A dermoscopic image of a skin lesion — 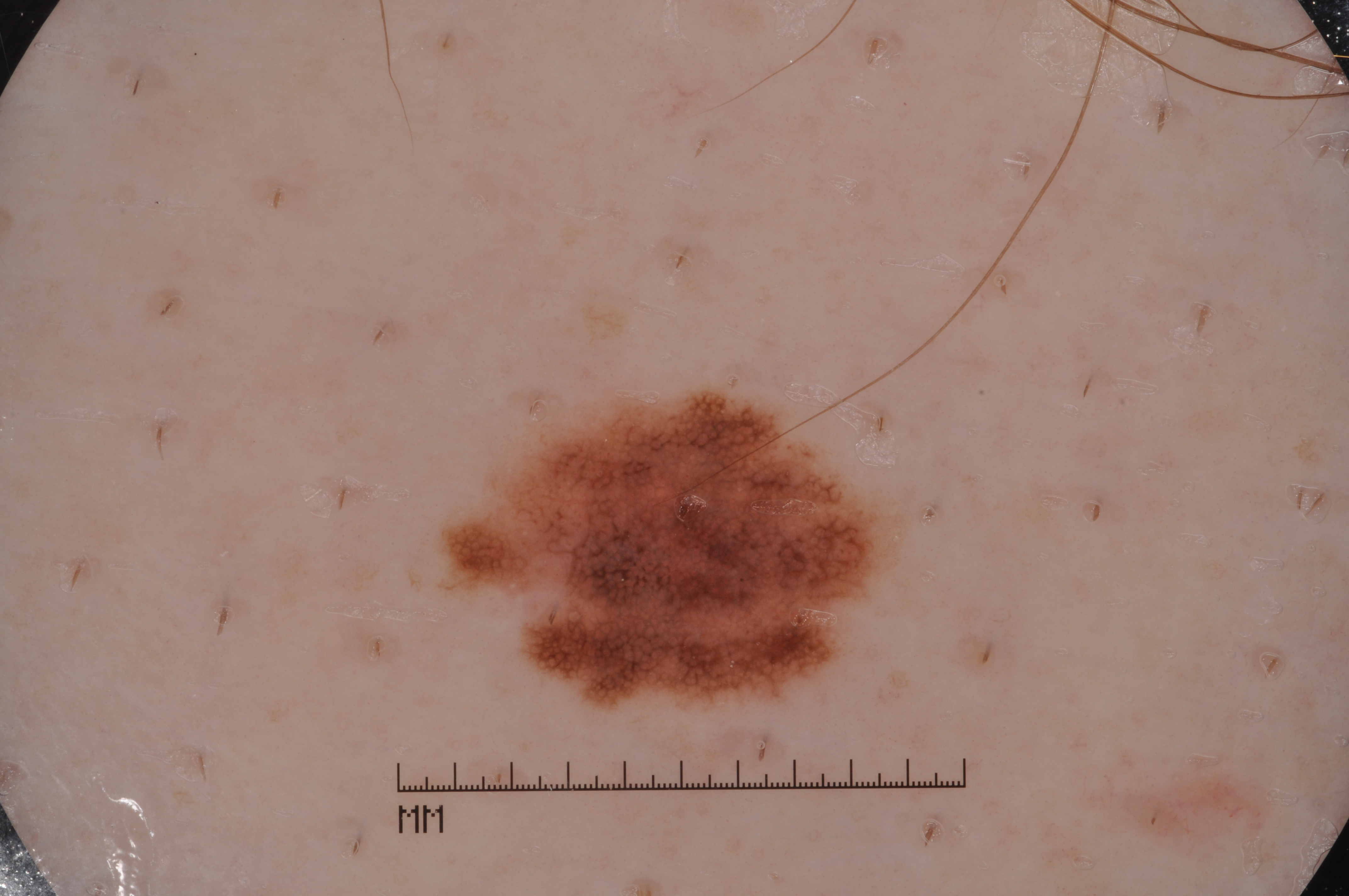| key | value |
|---|---|
| dermoscopic features | milia-like cysts and pigment network |
| lesion location | x1=453 y1=393 x2=885 y2=700 |
| assessment | a melanocytic nevus, a benign lesion |